An image taken at an angle:
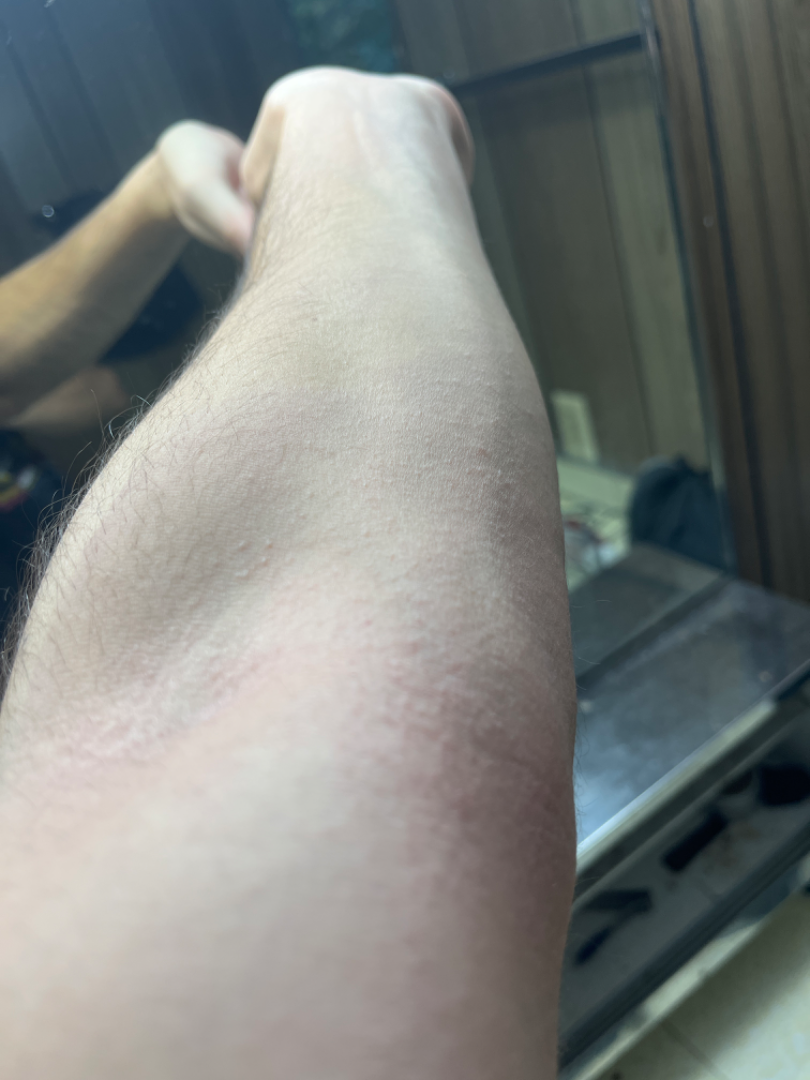Most consistent with Eczema.